A dermoscopy image of a single skin lesion.
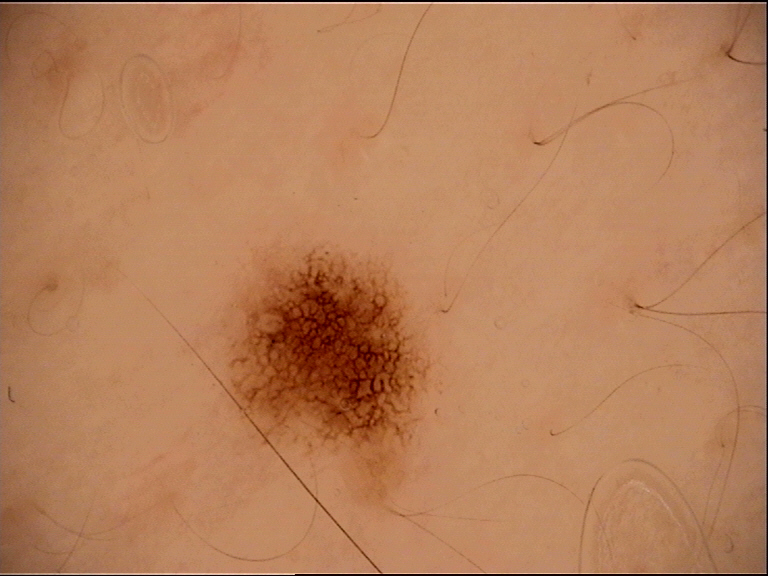Labeled as a dysplastic junctional nevus.